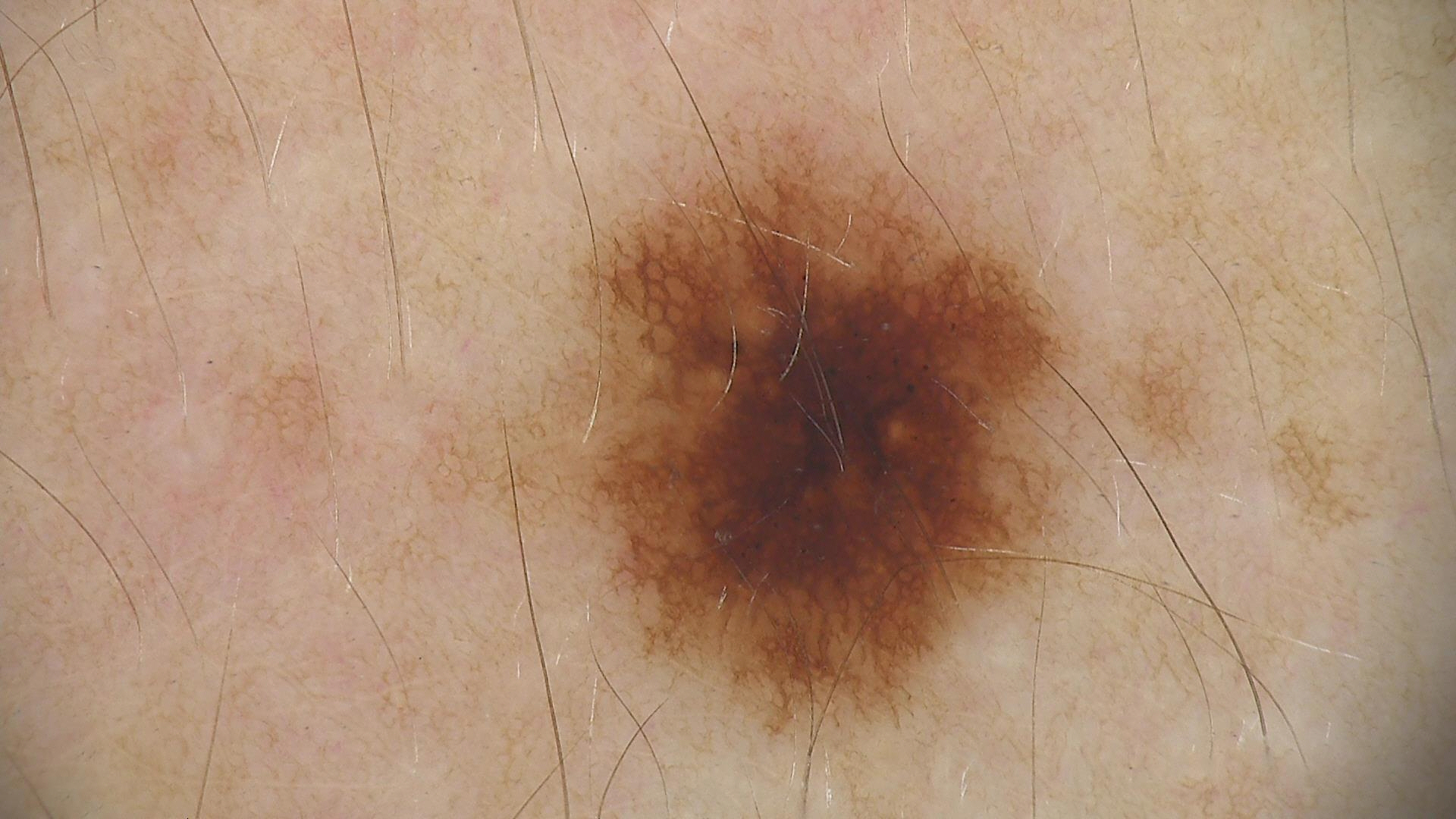imaging=dermoscopy
diagnostic label=dysplastic junctional nevus (expert consensus)